A dermoscopic image of a skin lesion:
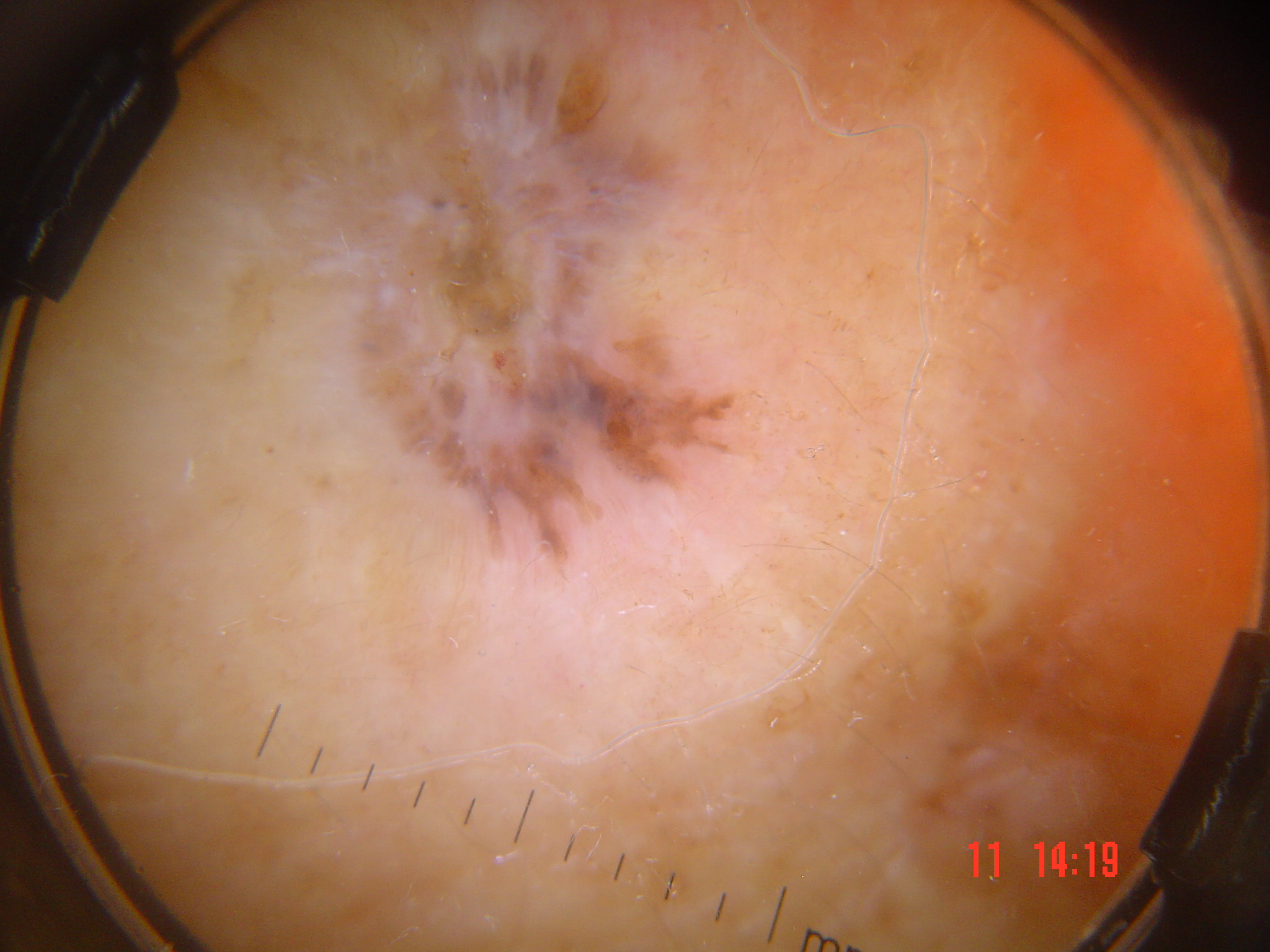pathology: basal cell carcinoma (biopsy-proven).